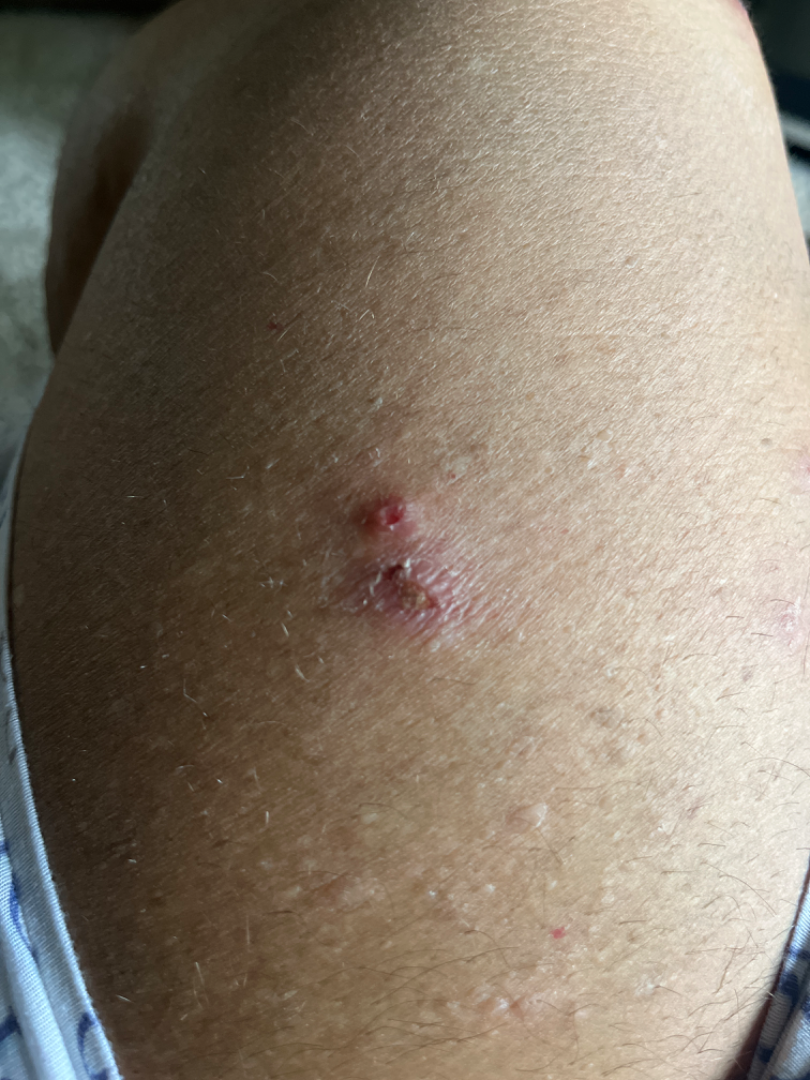assessment = ungradable on photographic review | surface texture = fluid-filled and raised or bumpy | self-categorized as = a rash | symptom duration = one to four weeks | framing = close-up | body site = leg | contributor = female, age 50–59.